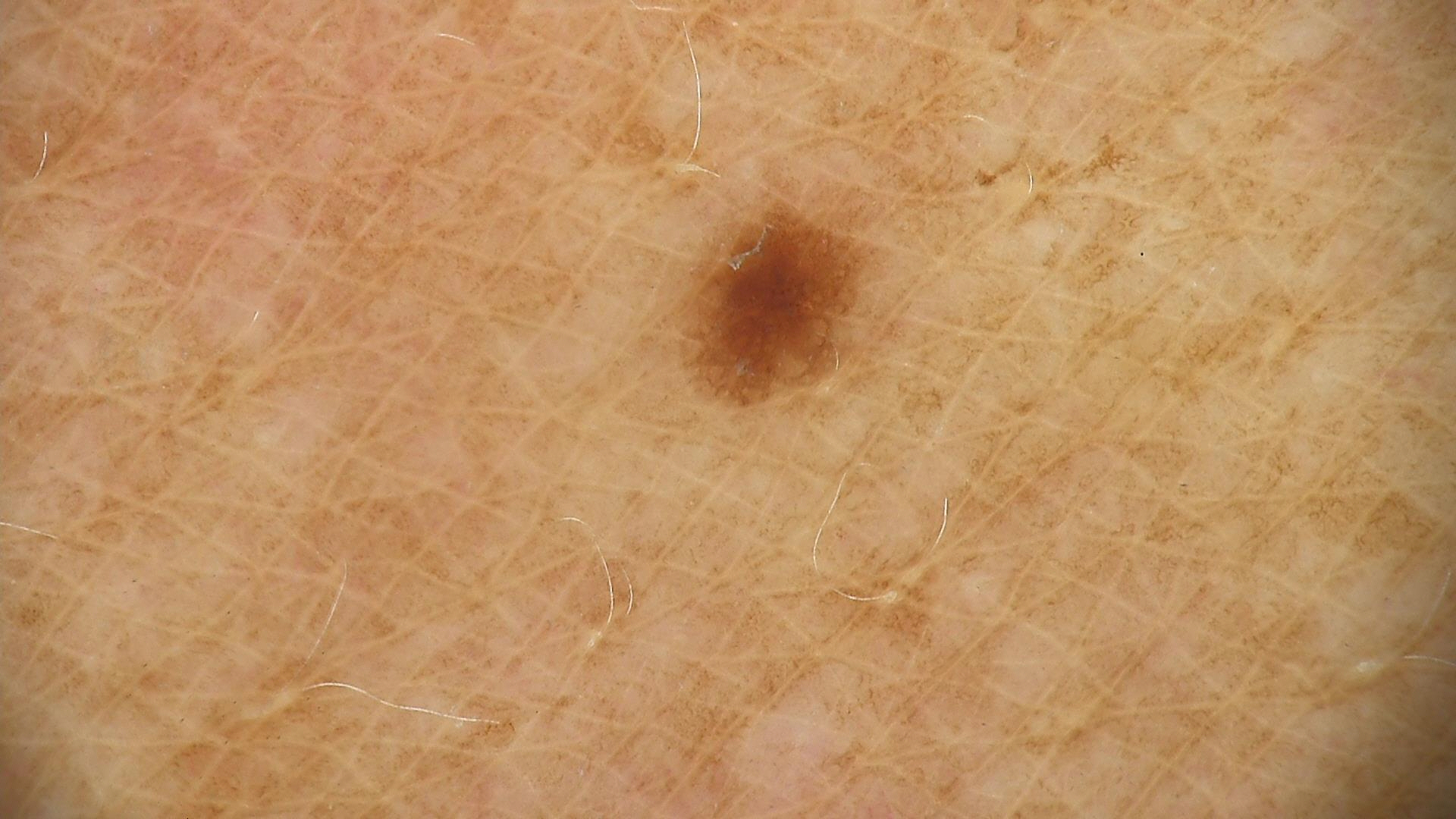Findings:
– label · junctional nevus (expert consensus)